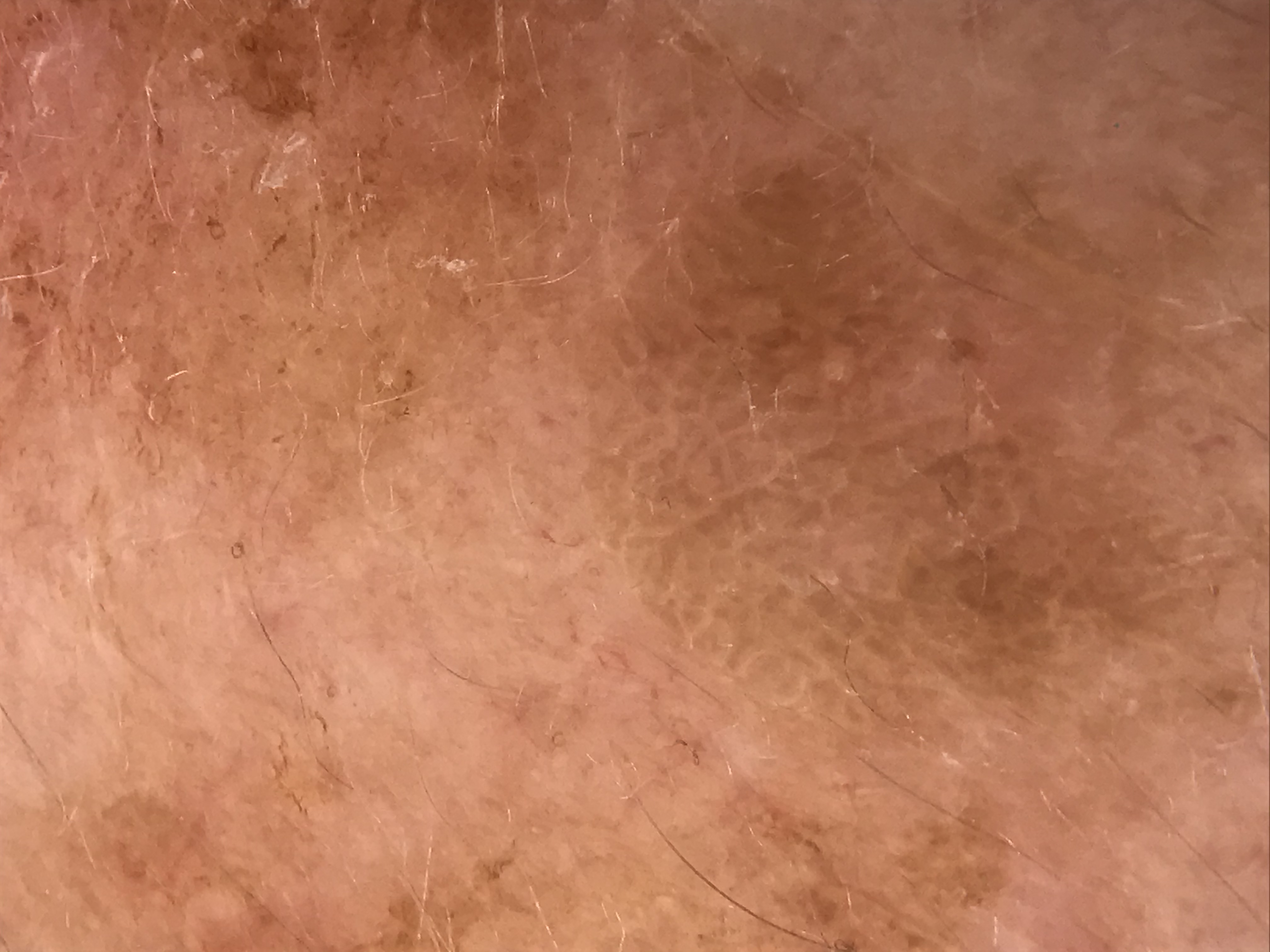A dermoscopy image of a single skin lesion. This is a keratinocytic lesion. Consistent with a seborrheic keratosis.